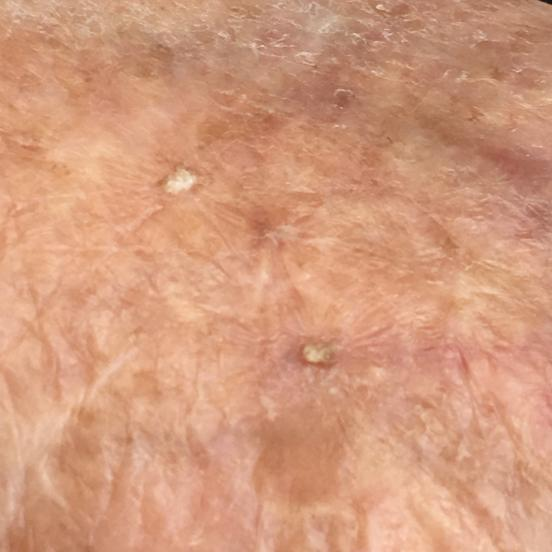Conclusion:
Diagnosed by dermatologist consensus as an actinic keratosis.